The chart records alcohol use and prior skin cancer (patient or family) · a male patient in their 30s · the patient was assessed as Fitzpatrick skin type II · a clinical photograph showing a skin lesion.
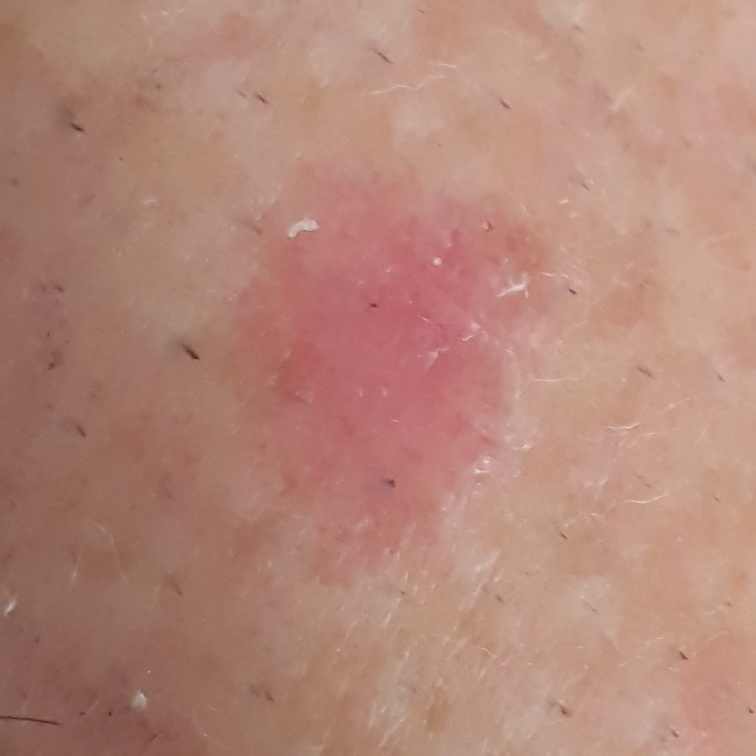body site — a forearm
size — 9x7 mm
patient-reported symptoms — elevation
pathology — basal cell carcinoma (biopsy-proven)